A macroscopic clinical photograph of a skin lesion · imaged for a research study, with no referral diagnosis recorded · a female subject 26 years of age: 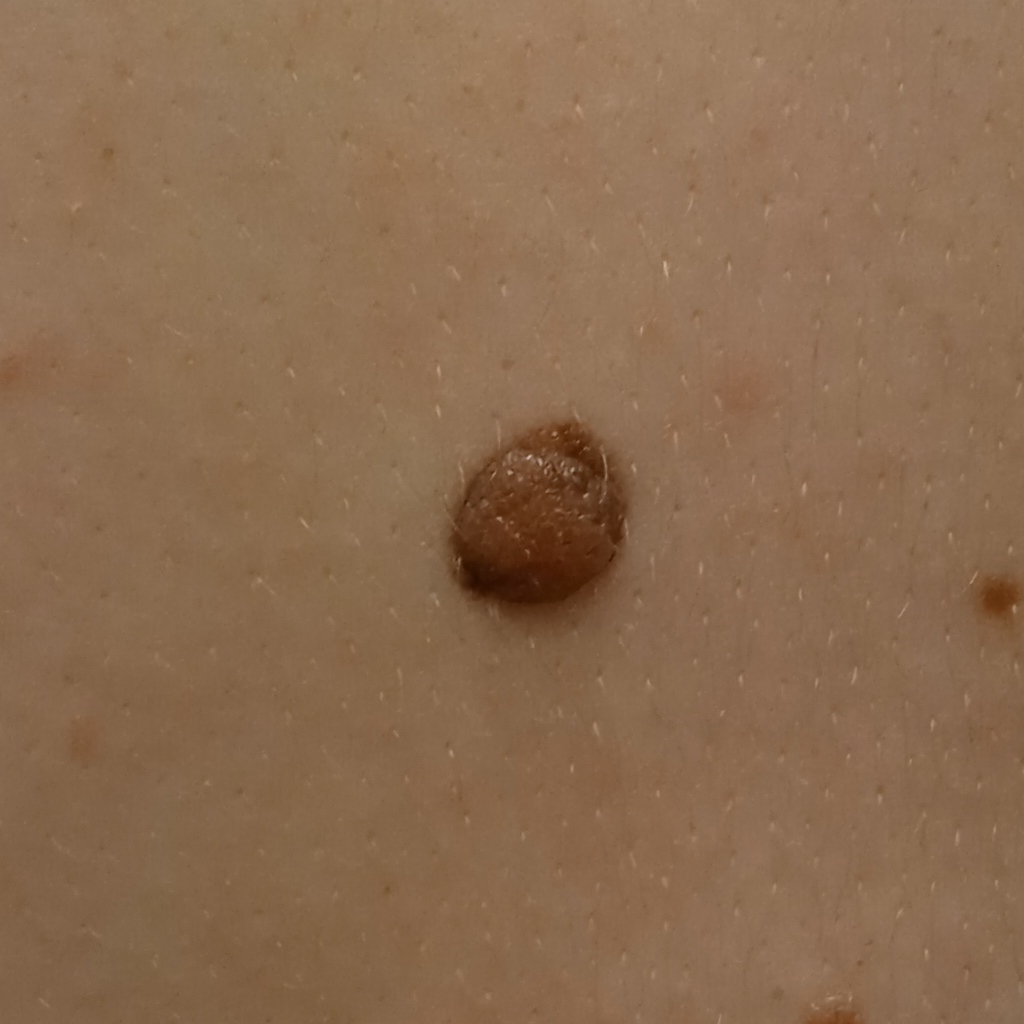The lesion measures approximately 8.9 mm.
The lesion was assessed as a melanocytic nevus.